Reported duration is one to four weeks · an image taken at a distance · the patient considered this skin that appeared healthy to them · the contributor reports the lesion is flat · located on the back of the hand, back of the torso, front of the torso and arm · reported lesion symptoms include bothersome appearance · male patient, age 40–49:
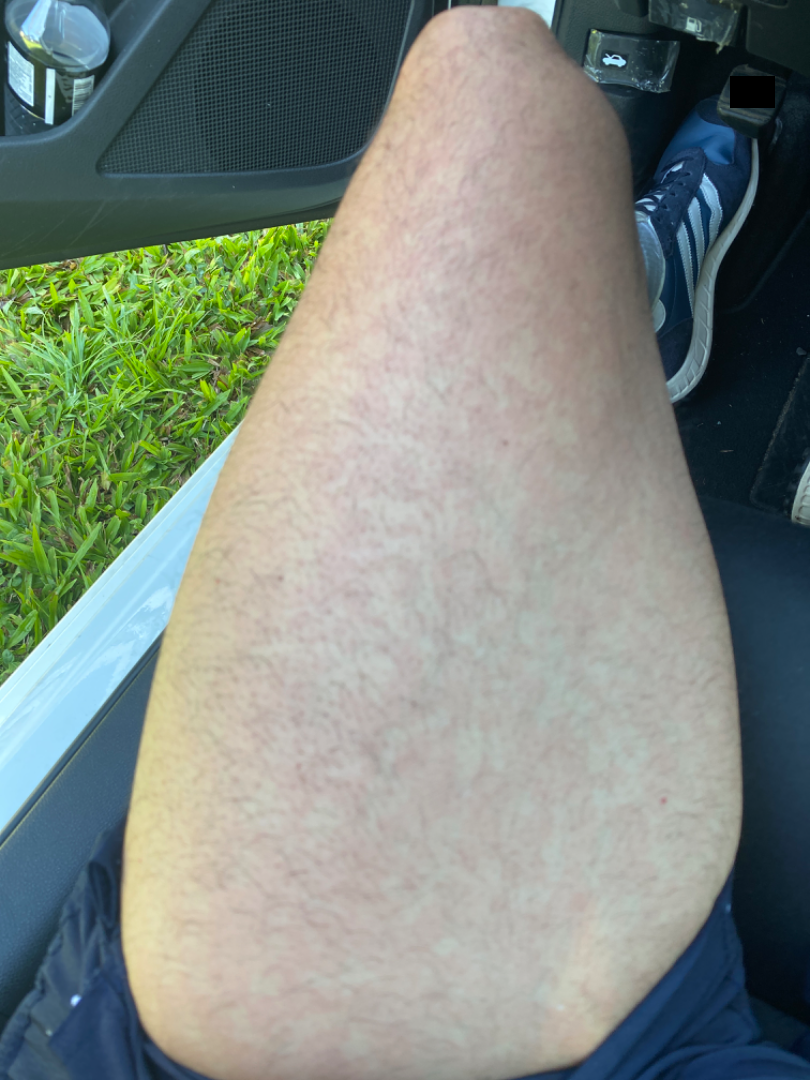Drug Rash (weight 0.31); Viral Exanthem (weight 0.24); Hypersensitivity (weight 0.12); Photodermatitis (weight 0.12); Irritant Contact Dermatitis (weight 0.12); Acute dermatitis, NOS (weight 0.10).